A skin lesion imaged with a dermatoscope:
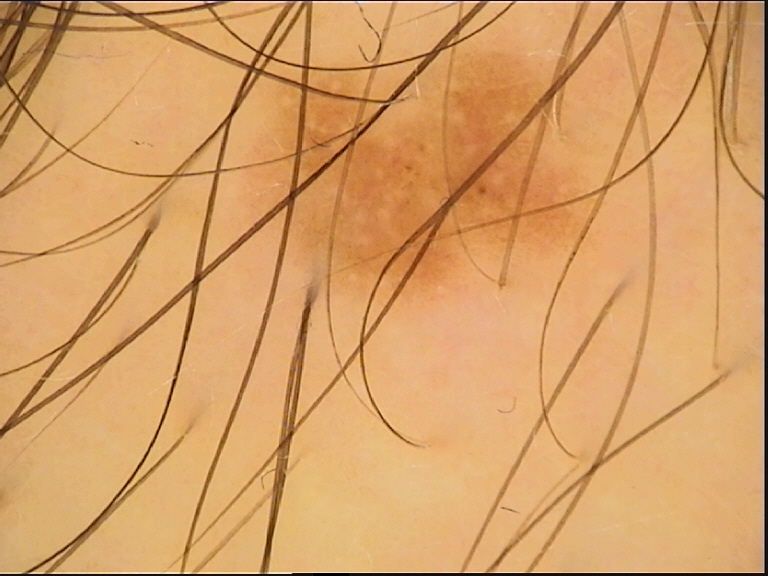class: dysplastic junctional nevus (expert consensus).